A dermoscopic photograph of a skin lesion:
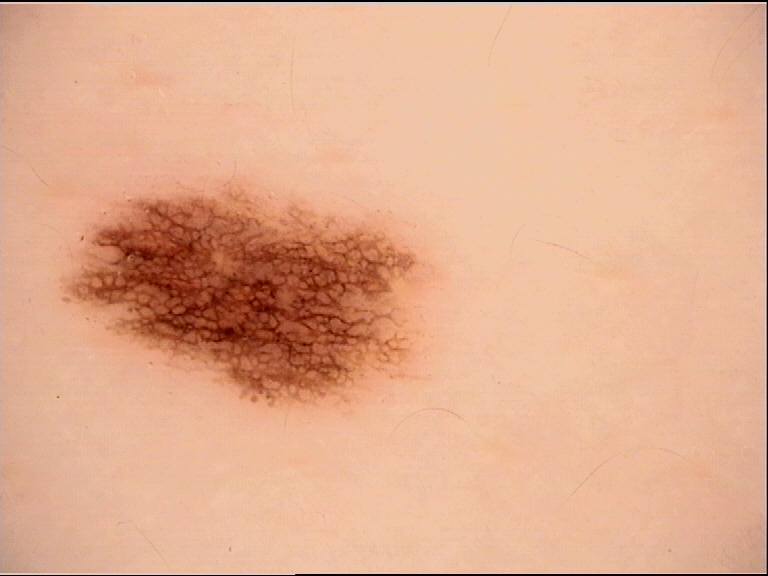Labeled as a benign lesion — a dysplastic junctional nevus.